A dermoscopic image of a skin lesion:
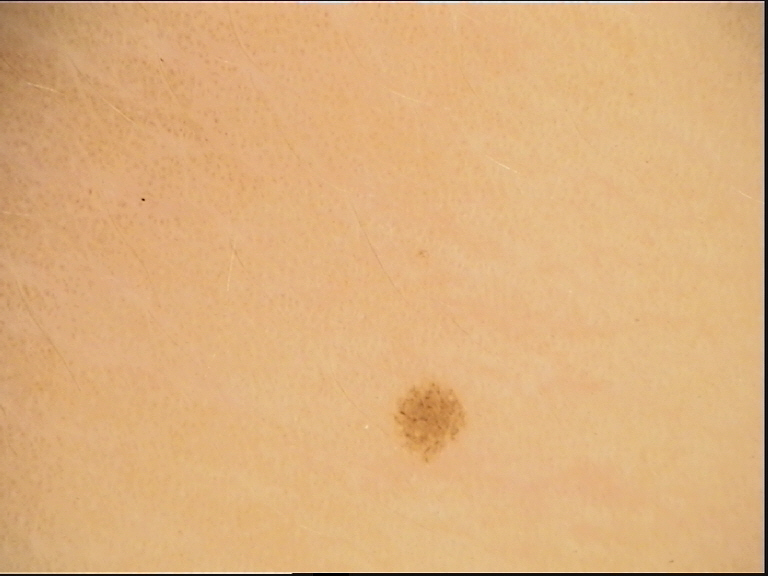Q: What is this lesion?
A: junctional nevus (expert consensus)